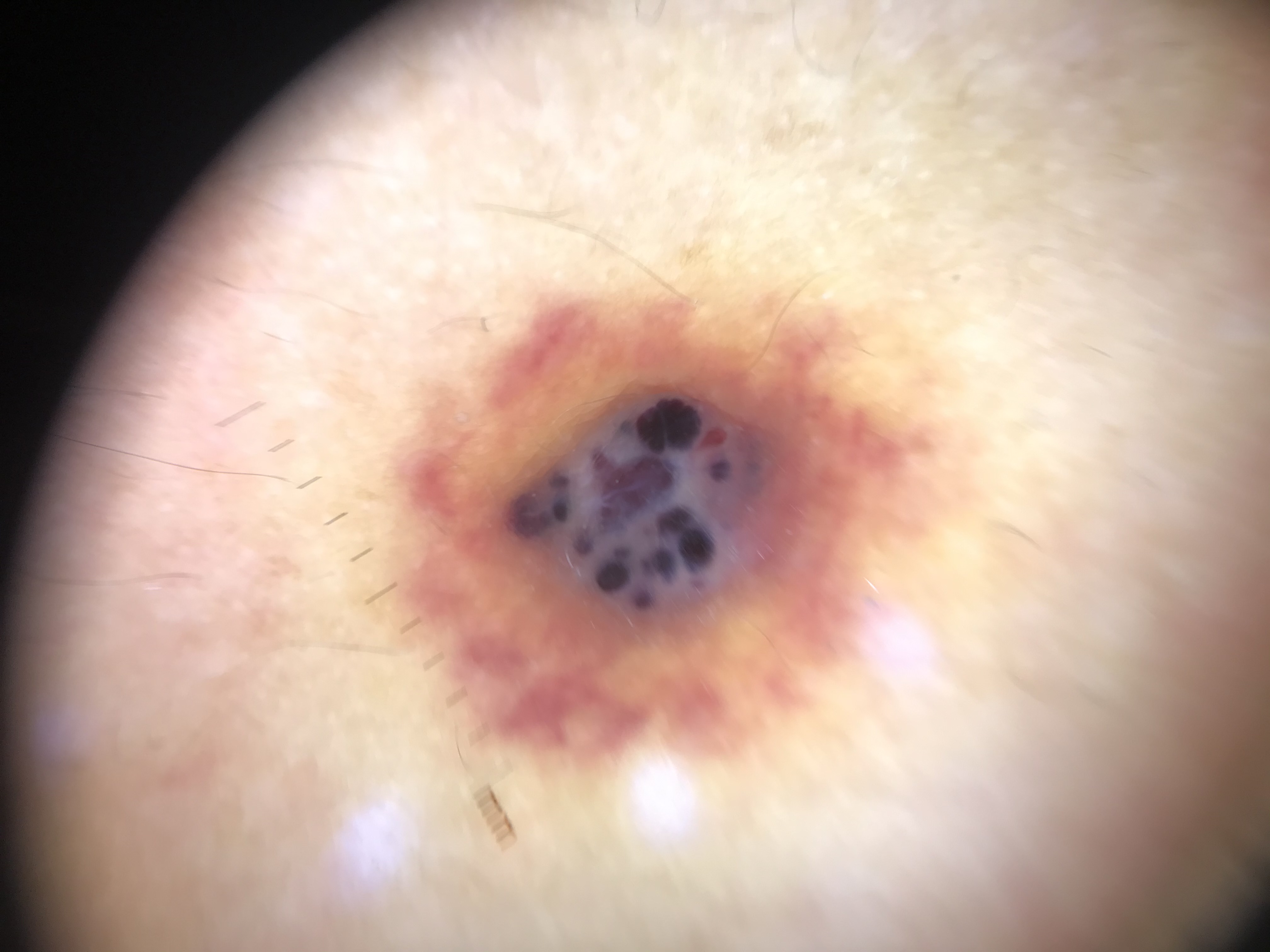A dermoscopic photograph of a skin lesion. Labeled as a vascular lesion — an angiokeratoma.